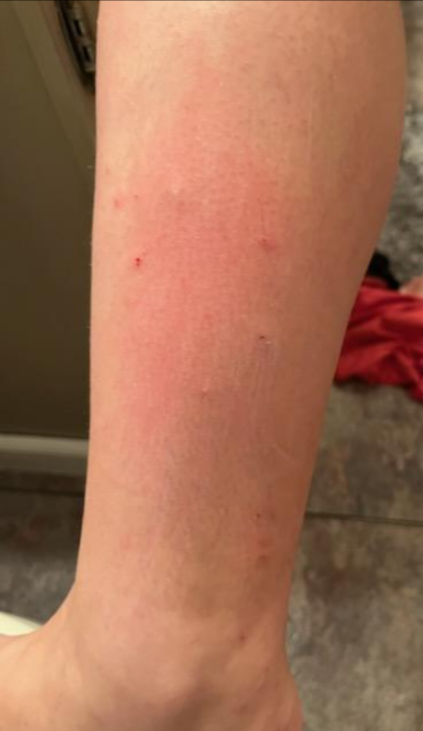shot type: close-up, differential: most consistent with Eczema.